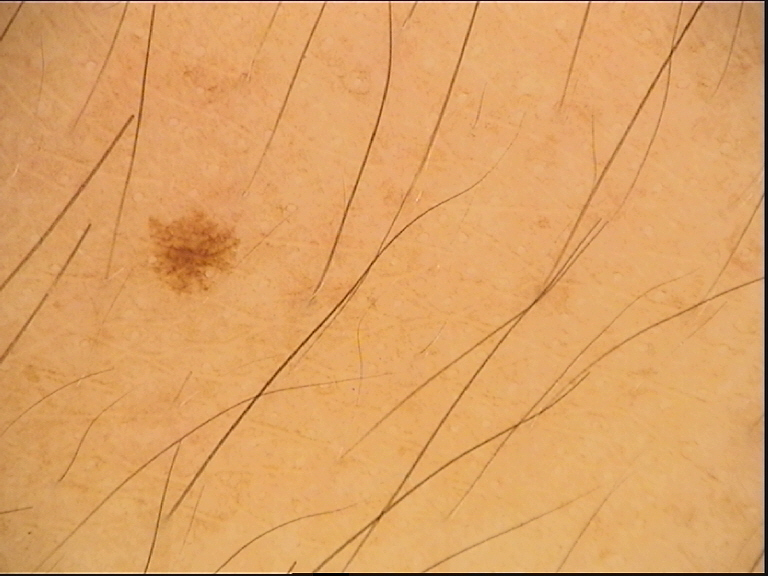Classified as a dysplastic junctional nevus.